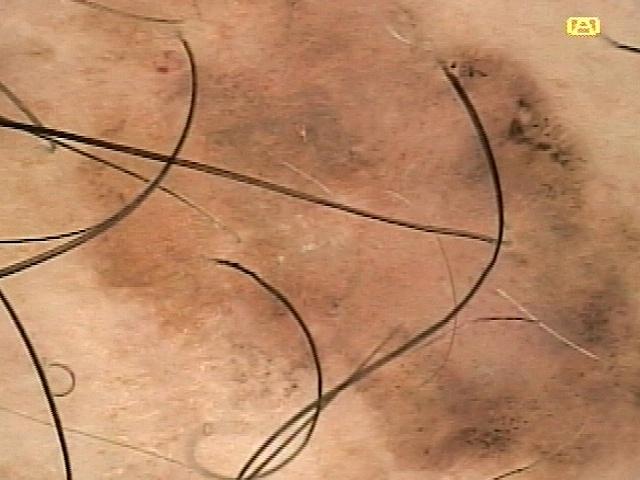Case:
– image · dermoscopic image
– Fitzpatrick · II
– location · an upper extremity
– pathology · Squamous cell carcinoma (biopsy-proven)